A patient 73 years old; a clinical photograph of a skin lesion:
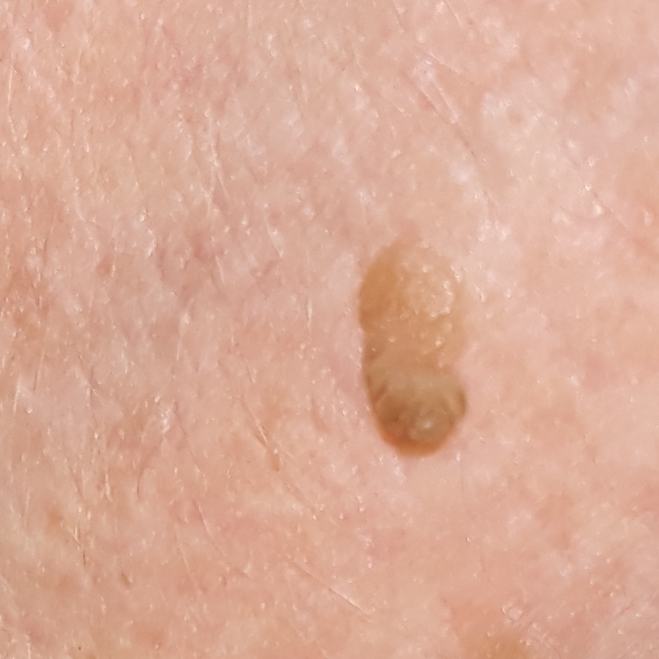• location — an arm
• impression — seborrheic keratosis (clinical consensus)